A dermoscopic image of a skin lesion:
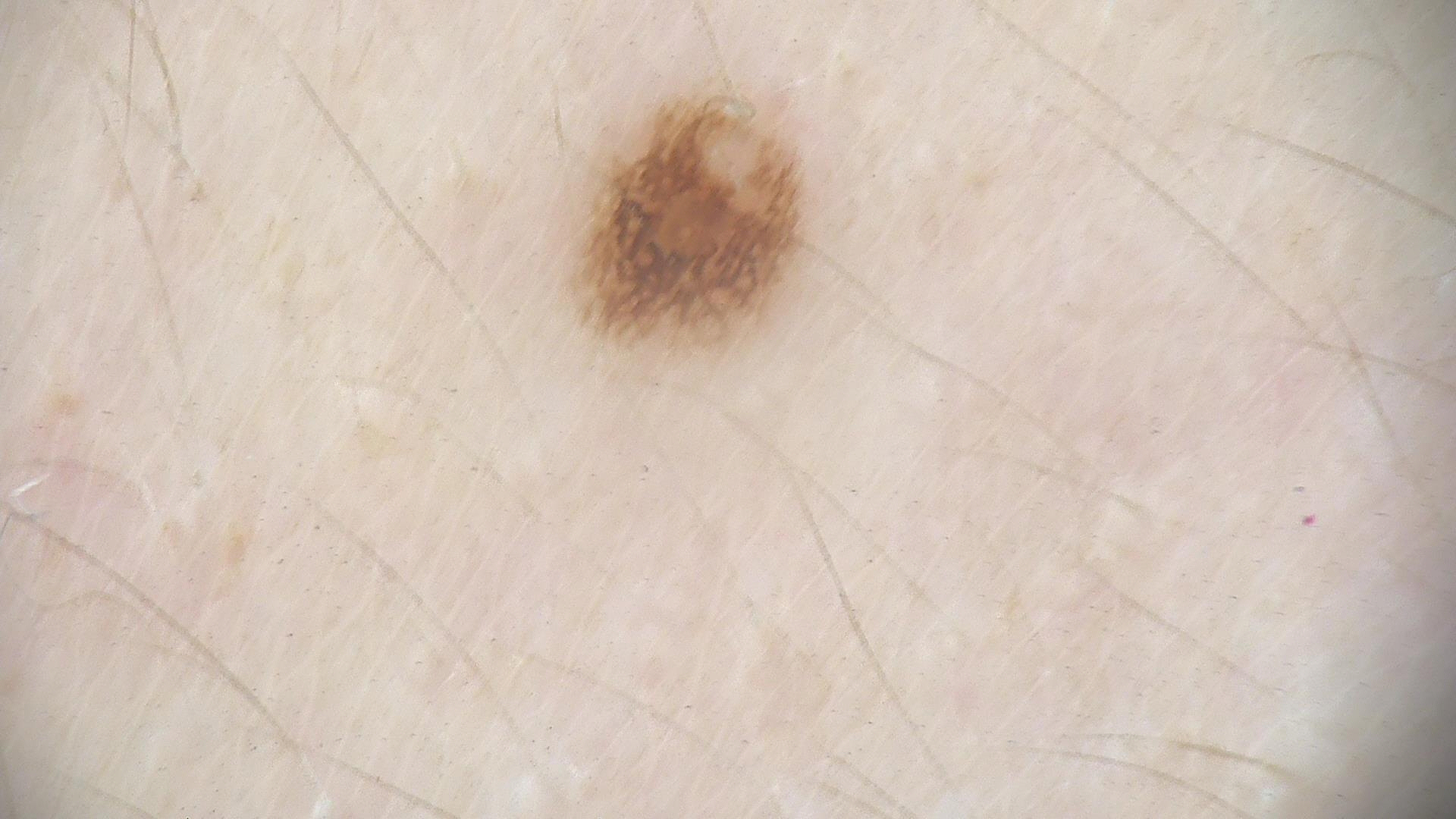The diagnosis was a benign lesion — a dysplastic junctional nevus.